A dermoscopic photograph of a skin lesion.
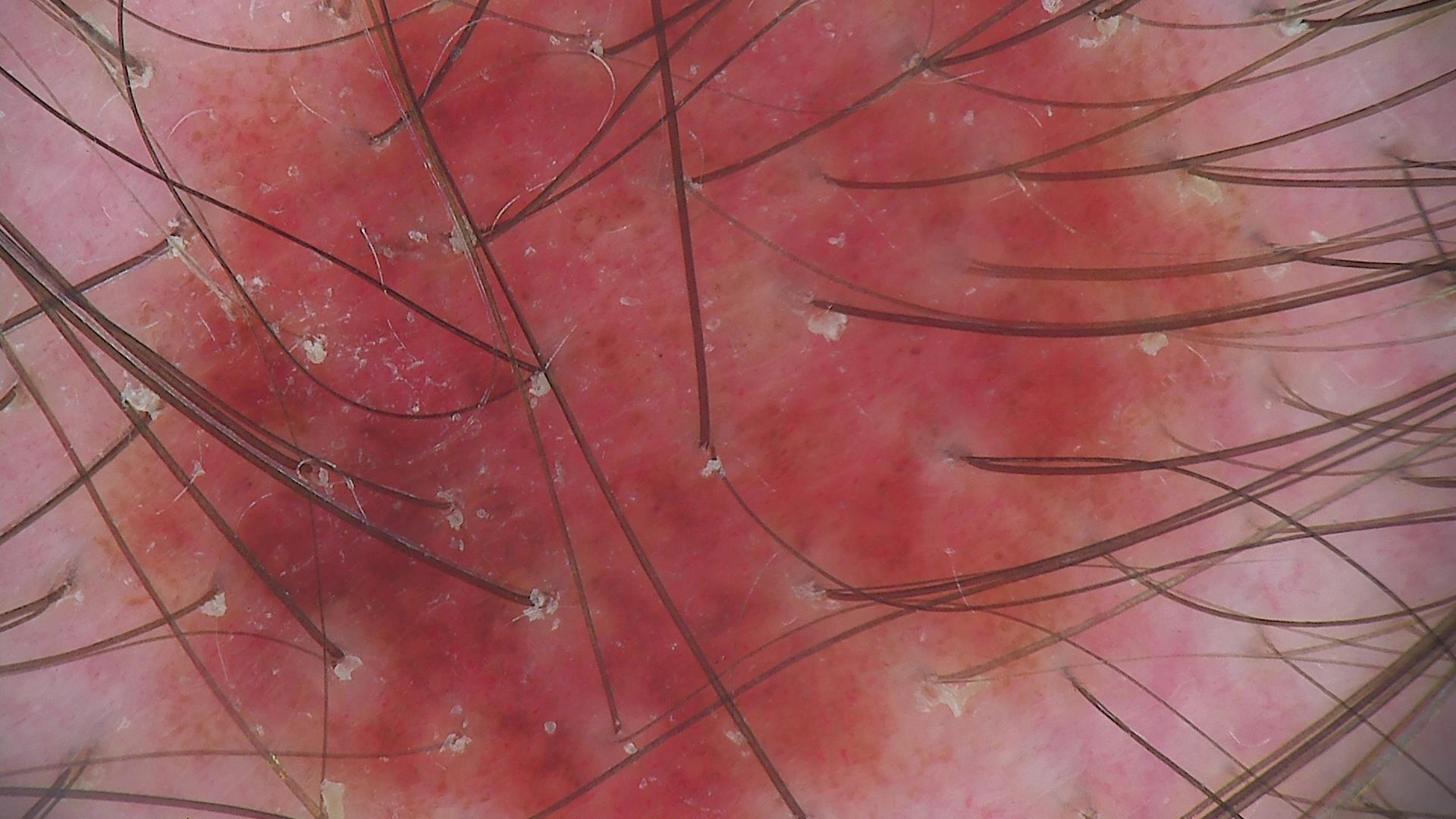<dermoscopy>
<diagnosis>
<name>dysplastic compound nevus</name>
<code>cd</code>
<malignancy>benign</malignancy>
<super_class>melanocytic</super_class>
<confirmation>expert consensus</confirmation>
</diagnosis>
</dermoscopy>